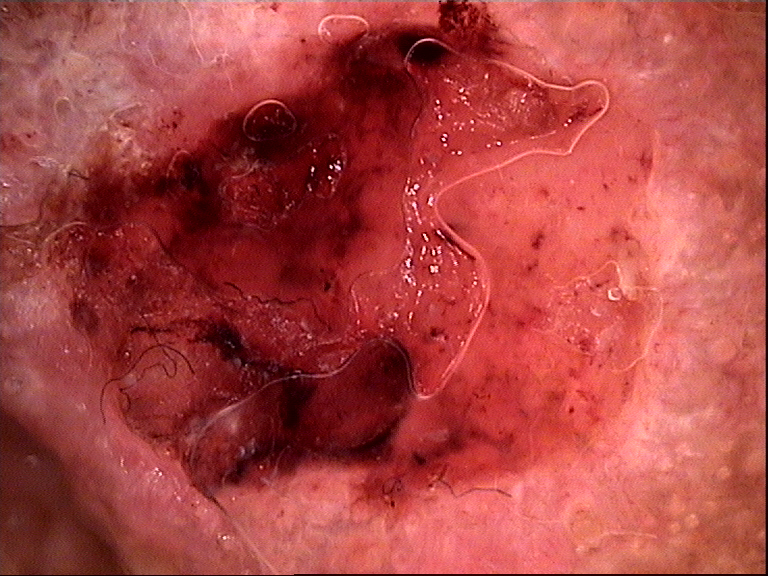The biopsy diagnosis was a keratinocytic lesion — a squamous cell carcinoma.